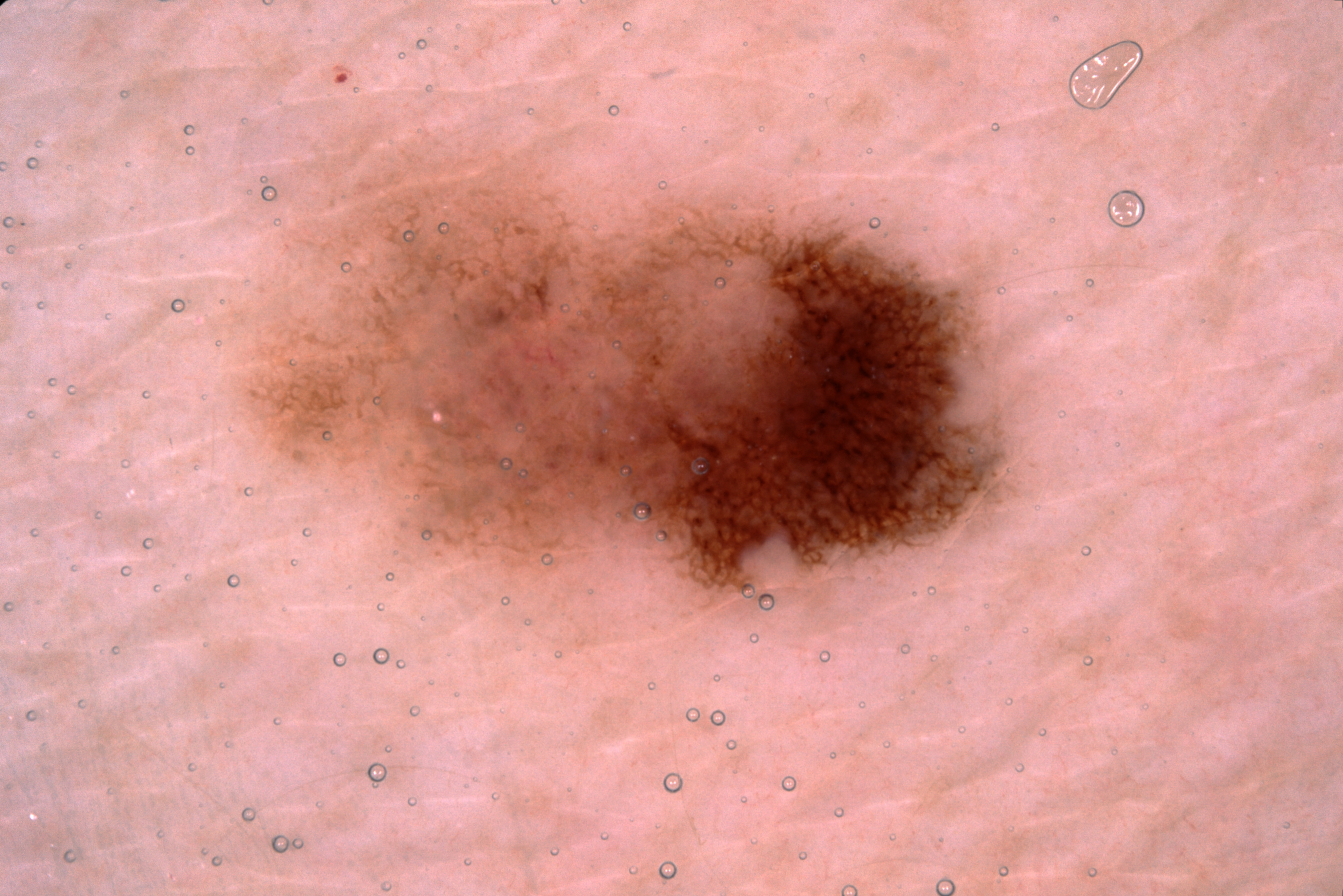A dermoscopic view of a skin lesion. The patient is a female aged 48 to 52. On dermoscopy, the lesion shows pigment network; no streaks, negative network, or milia-like cysts. In (x1, y1, x2, y2) order, the visible lesion spans [245,149,1019,613]. Expert review diagnosed this as a melanocytic nevus, a benign lesion.